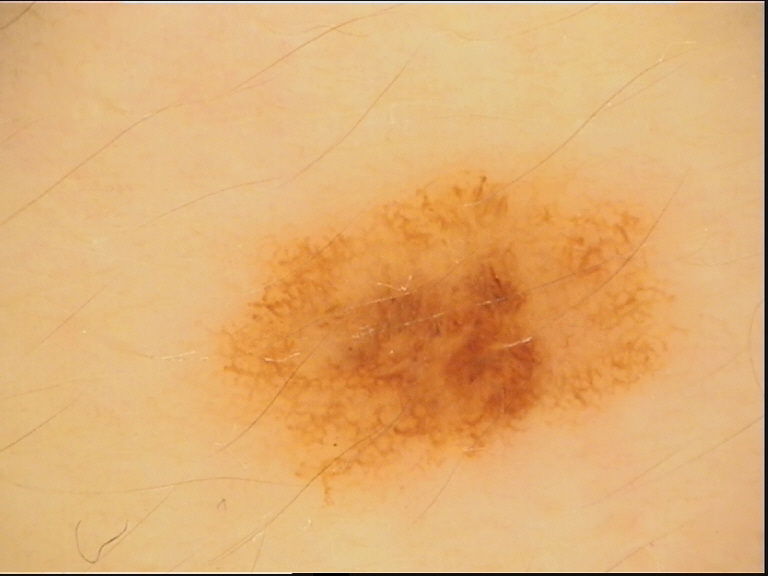- class · dysplastic junctional nevus (expert consensus)